Close-up view: 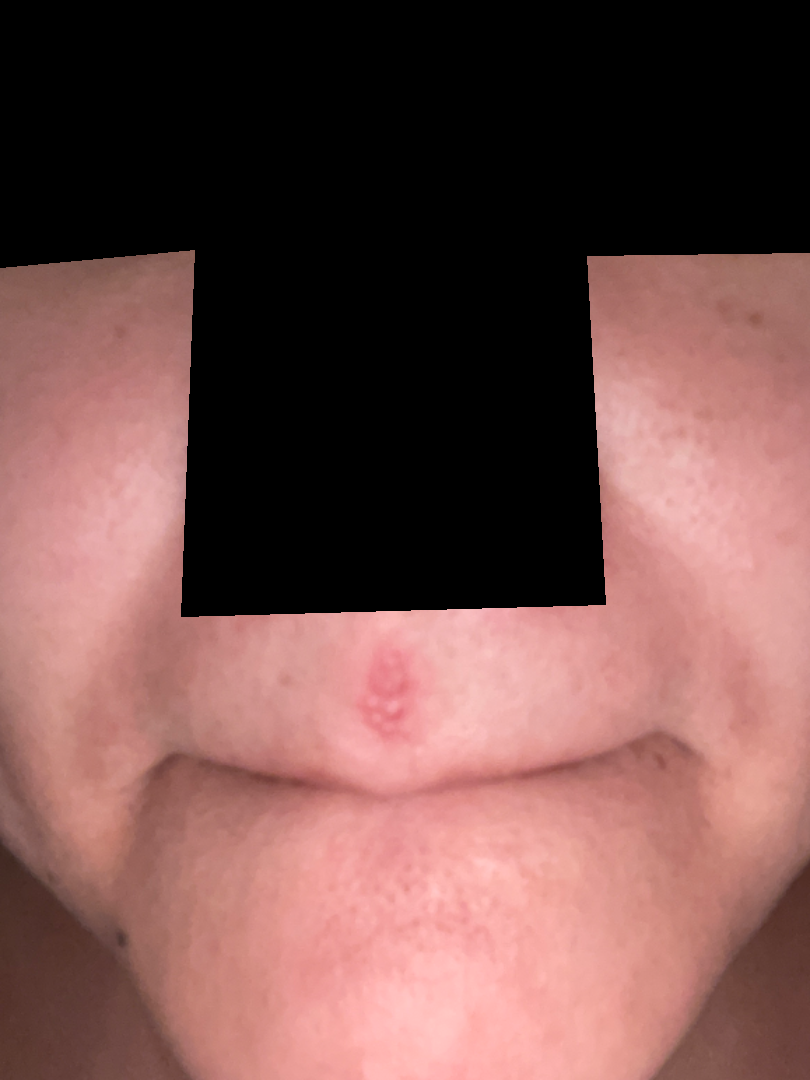The case was difficult to assess from the available photograph.